The patient is female, the lesion involves the arm and front of the torso, the patient notes the condition has been present for less than one week, the lesion is associated with bothersome appearance, this is a close-up image: 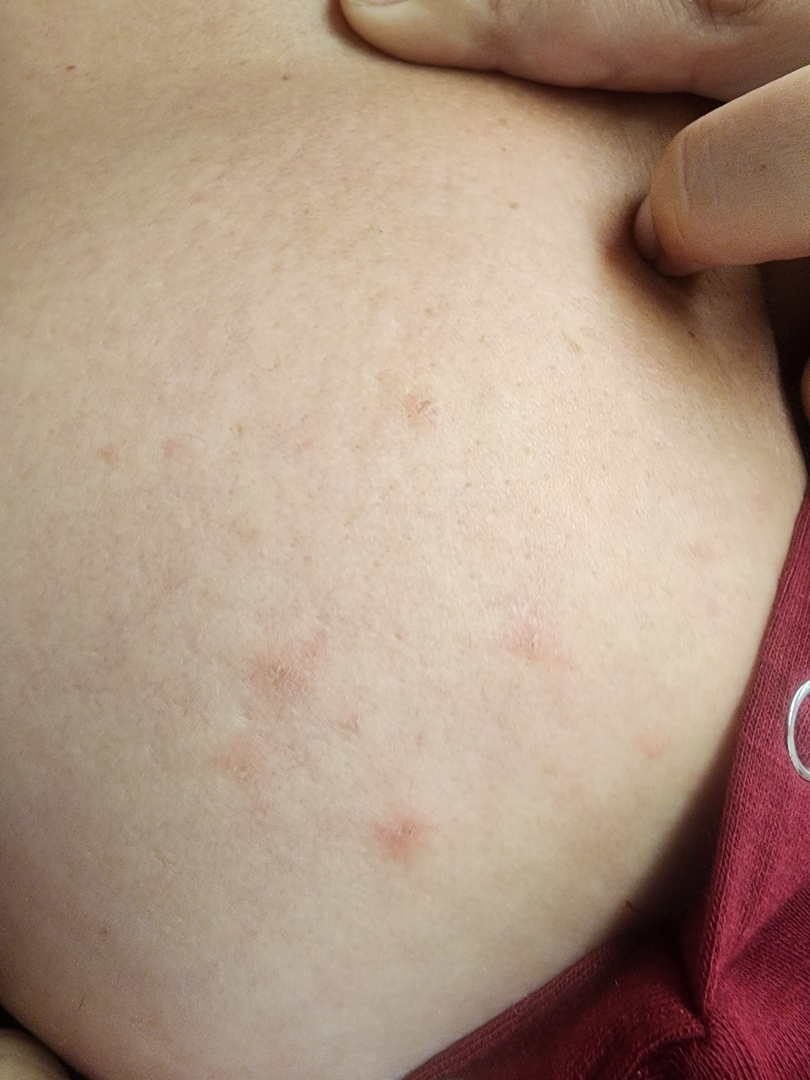assessment: indeterminate from the photograph